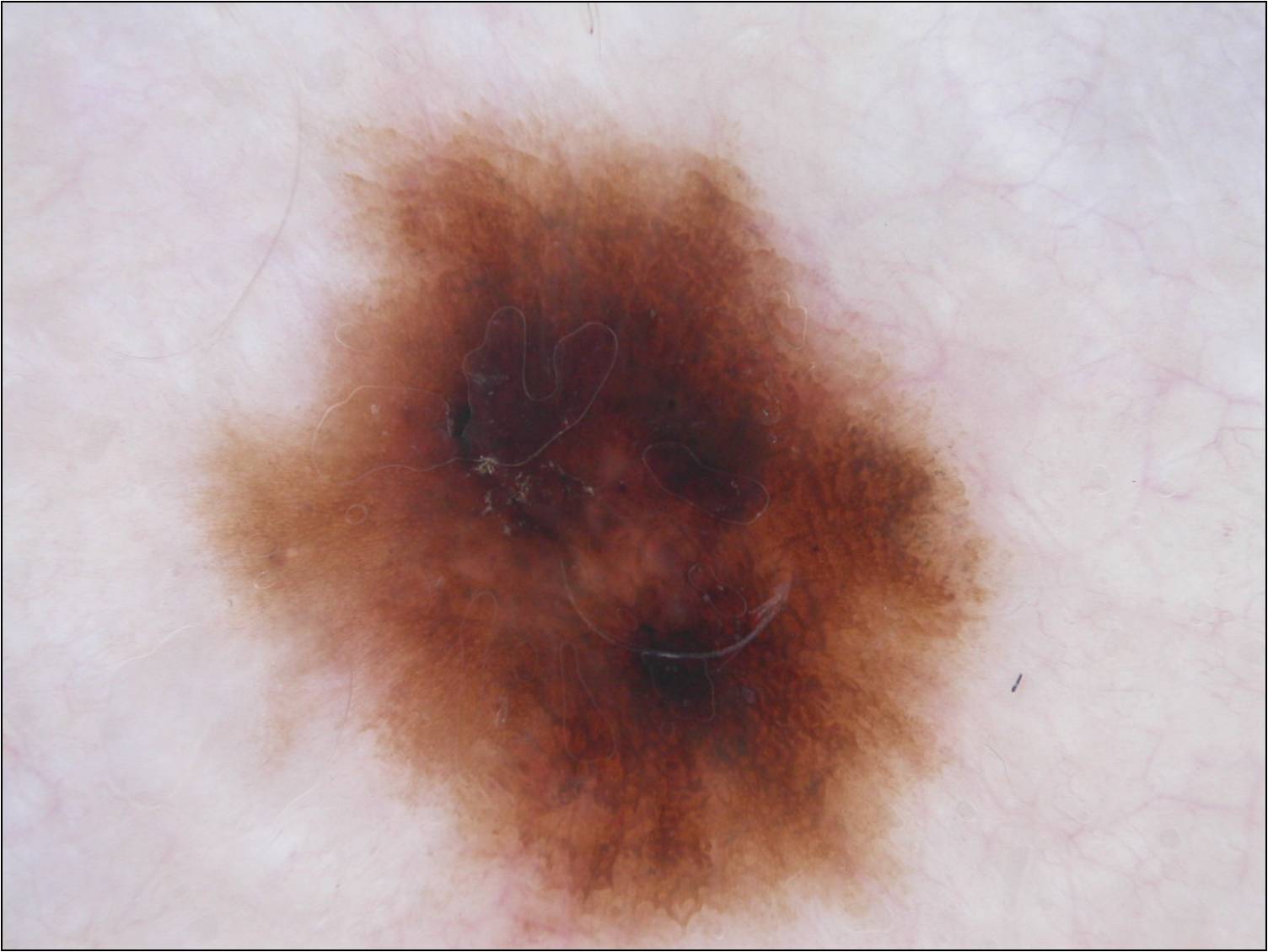modality=dermoscopy of a skin lesion
subject=female, aged 43 to 47
dermoscopic findings=globules and pigment network
bounding box=178 98 1023 947
lesion size=~43% of the field
assessment=a melanocytic nevus